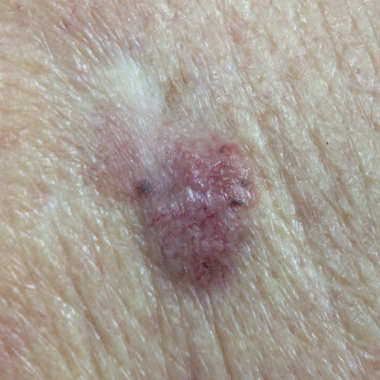Q: Patient demographics?
A: male, in their late 80s
Q: Skin phototype?
A: III
Q: Any relevant history?
A: prior malignancy (patient or family), pesticide exposure, tobacco use, alcohol use, no prior skin cancer (patient or family)
Q: What is the anatomic site?
A: the back
Q: What are the lesion's dimensions?
A: 17x10 mm
Q: Any reported symptoms?
A: itching, elevation
Q: What is the diagnosis?
A: basal cell carcinoma (biopsy-proven)